A male subject age 89. A dermatoscopic image of a skin lesion:
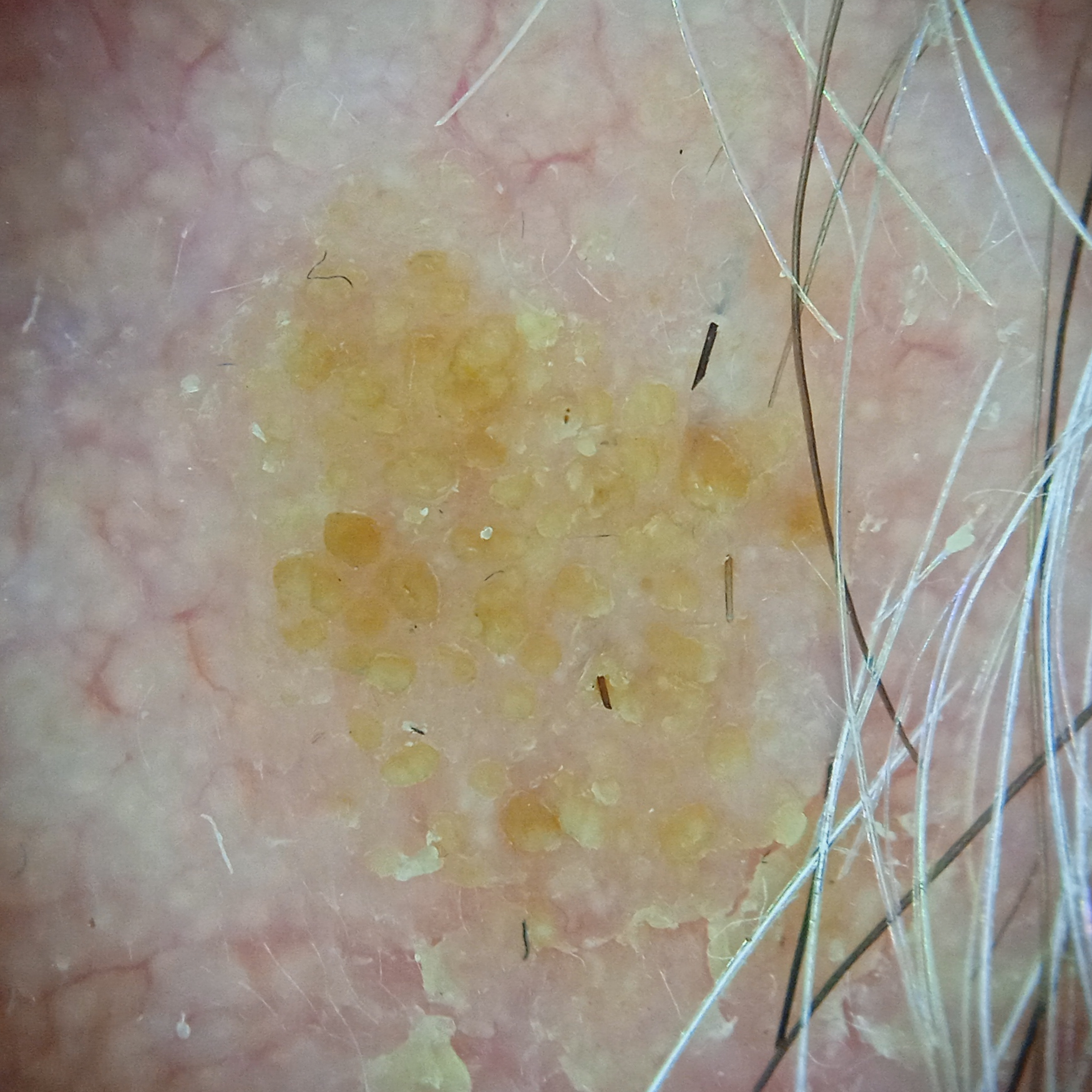Case summary: Located on the face. The lesion measures approximately 8.8 mm. Impression: The lesion was assessed as a seborrheic keratosis.